A female subject aged 73 to 77 · a clinical overview photograph of a skin lesion · the chart notes a previous melanoma · skin type II:
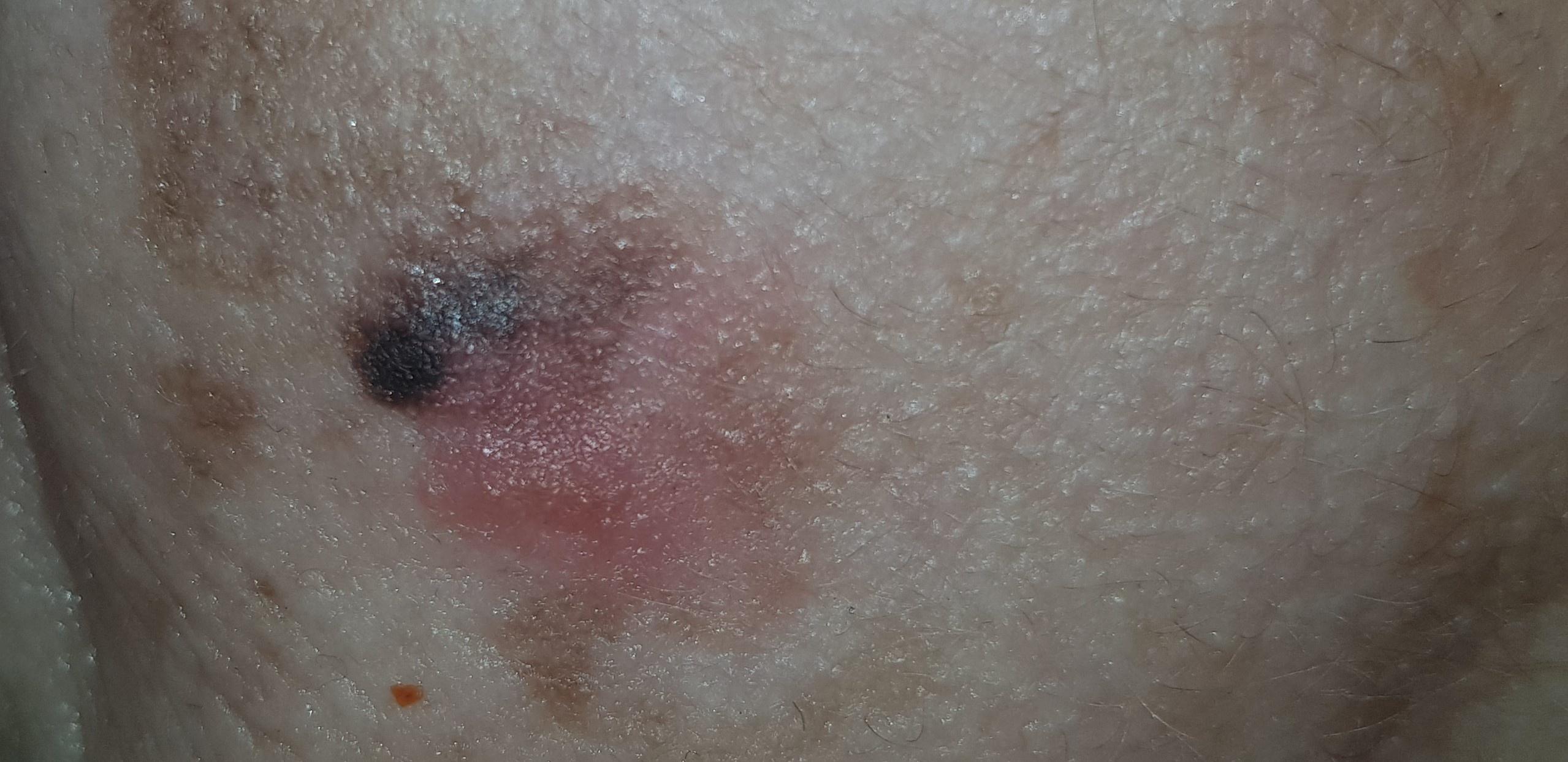Case summary:
The lesion involves the head or neck.
Pathology:
On biopsy, the diagnosis was a melanoma.